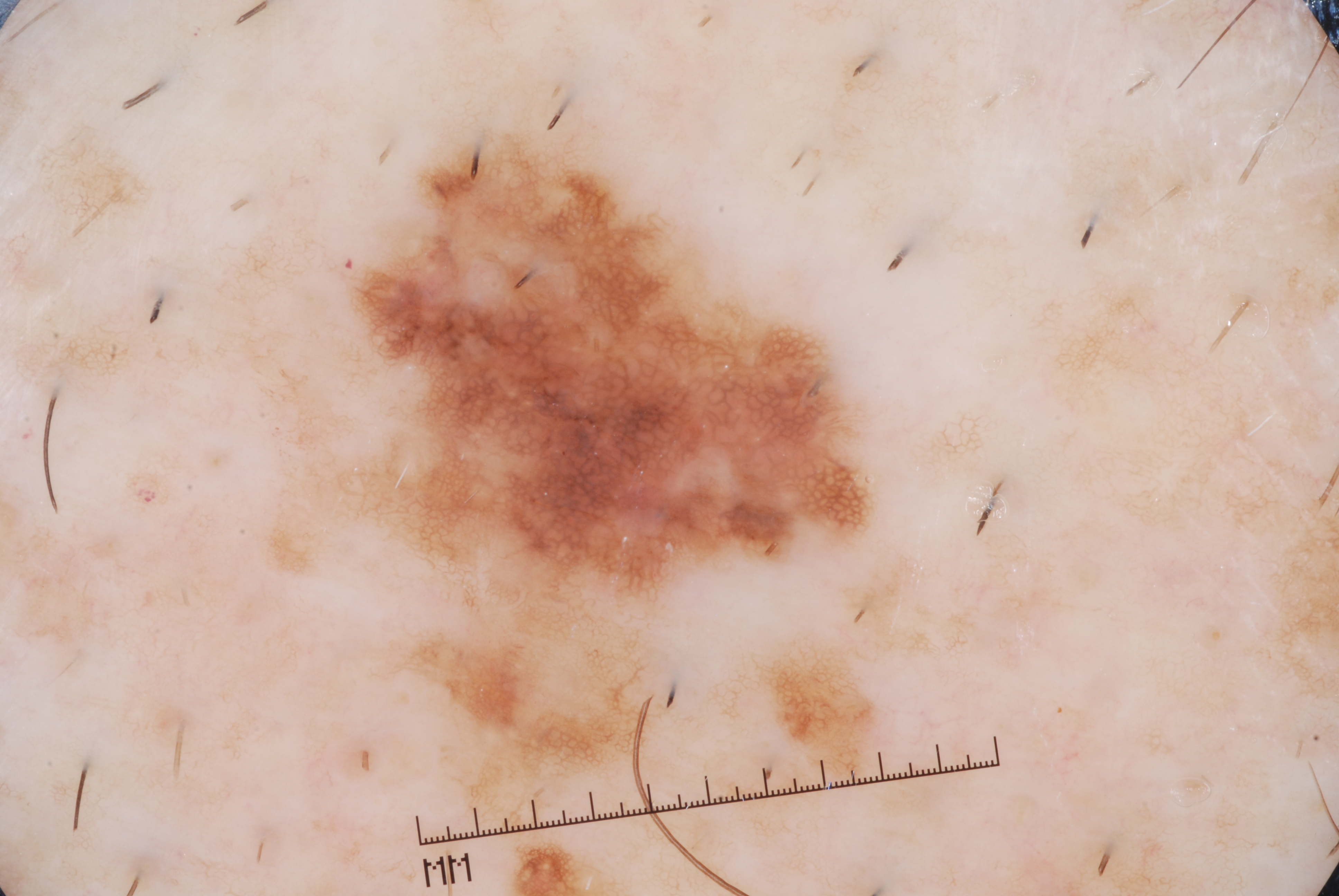patient — male, in their mid- to late 60s | modality — dermatoscopic image of a skin lesion | lesion extent — moderate | bounding box — bbox(356, 140, 868, 616) | dermoscopic pattern — milia-like cysts and pigment network; absent: negative network and streaks | diagnostic label — a melanoma.